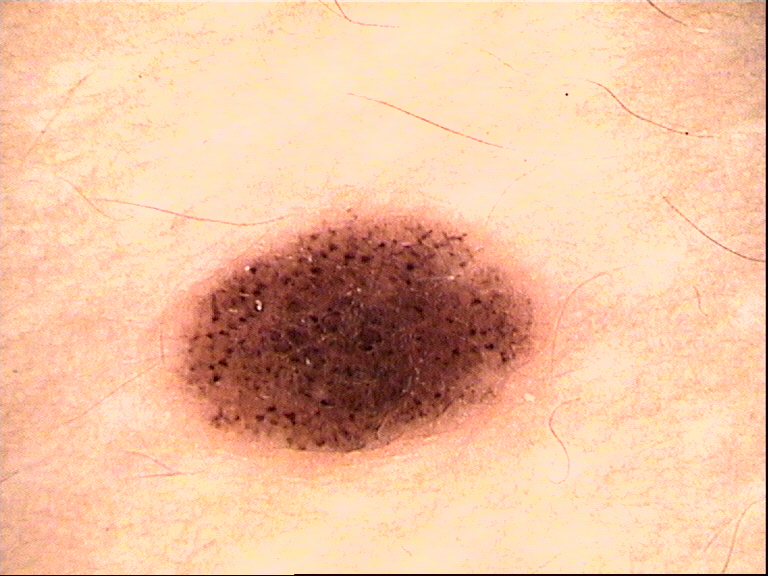Findings:
- diagnosis — compound nevus (expert consensus)